The photograph is a close-up of the affected area · the affected area is the palm.
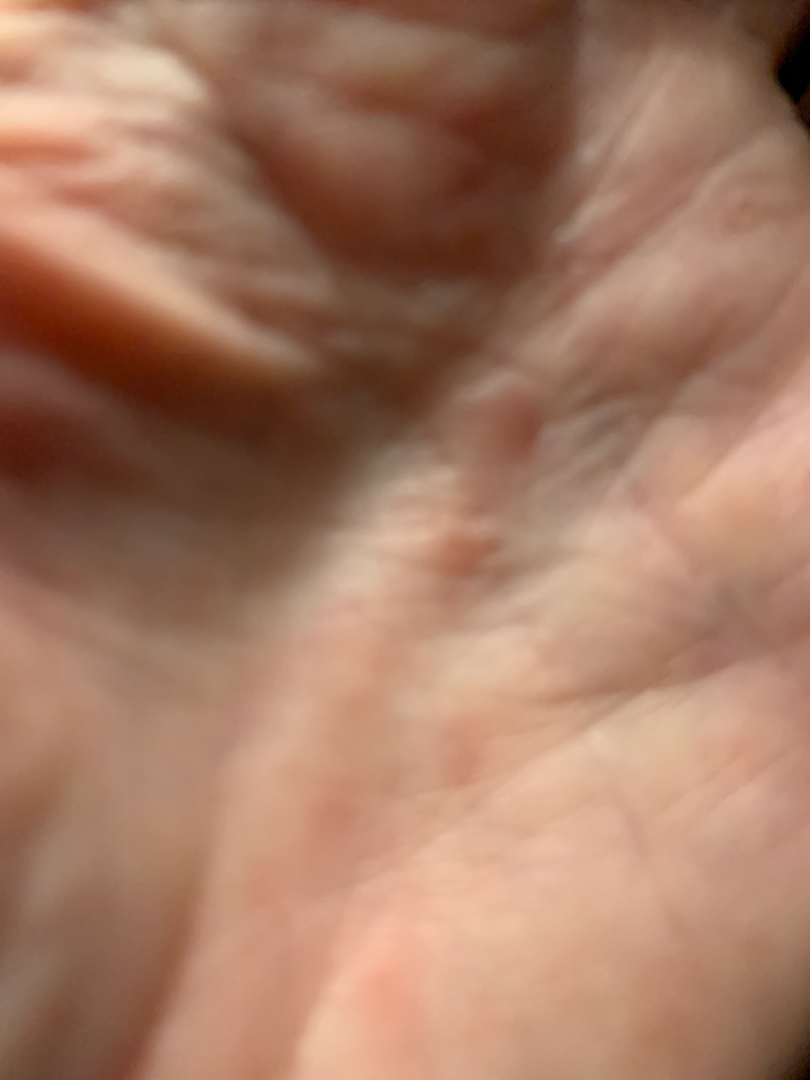<dermatology_case>
<texture>flat</texture>
<patient_category>a rash</patient_category>
<differential>
  <tied_lead>Eczema, Syphilis, Hand foot and mouth disease</tied_lead>
</differential>
</dermatology_case>